A clinical photo of a skin lesion taken with a smartphone.
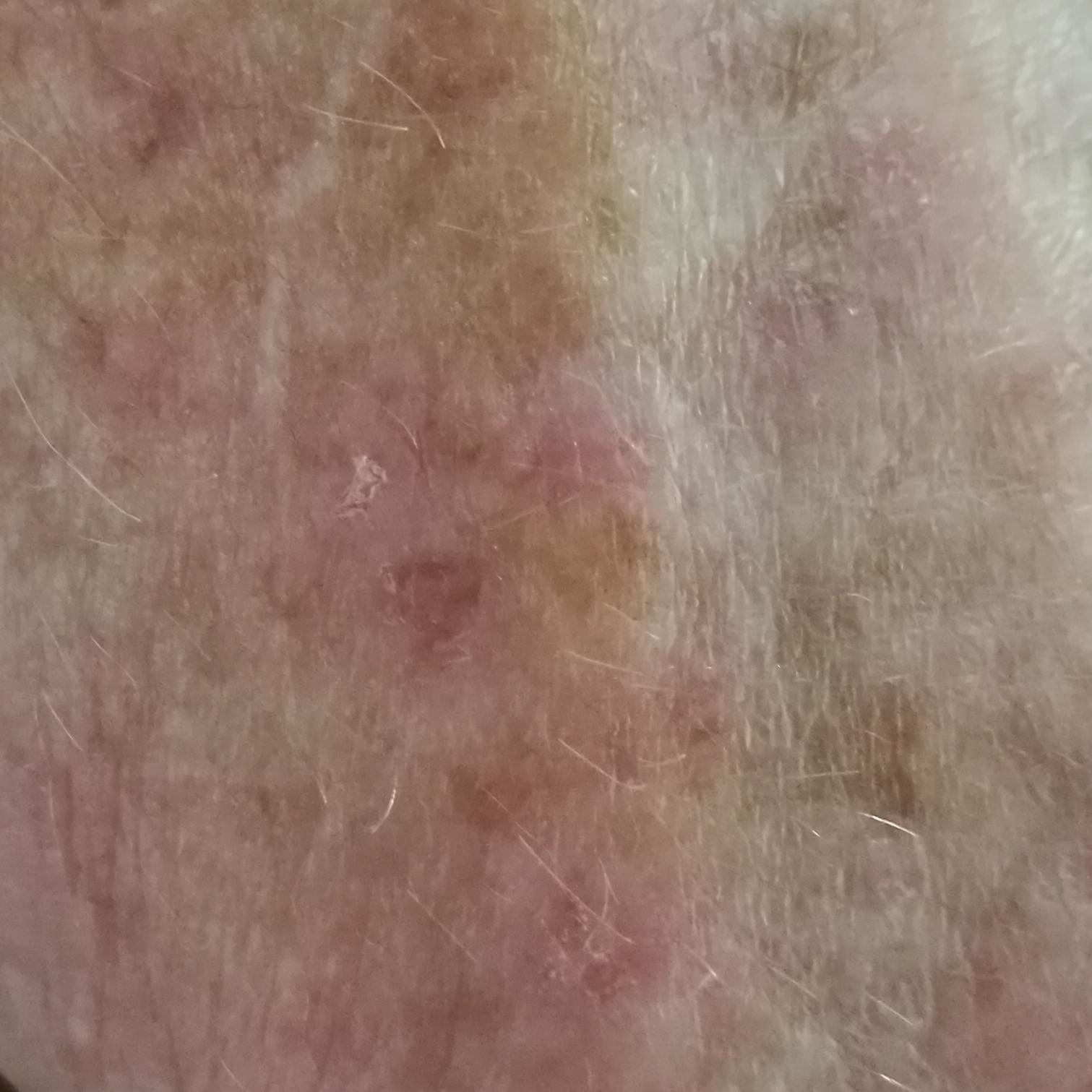Case summary: The lesion was found on a forearm. By the patient's account, the lesion itches. Conclusion: The clinical impression was a premalignant lesion — an actinic keratosis.